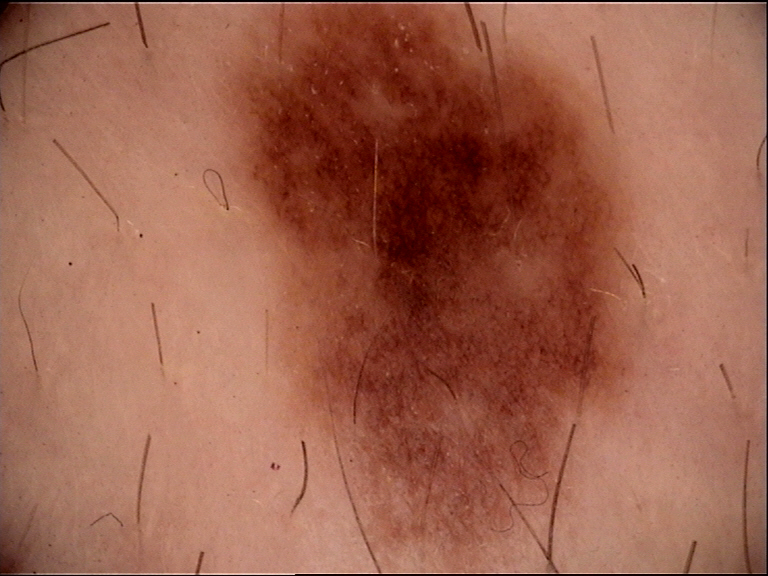image type = dermoscopy, class = dysplastic junctional nevus (expert consensus).